A dermoscopic photograph of a skin lesion.
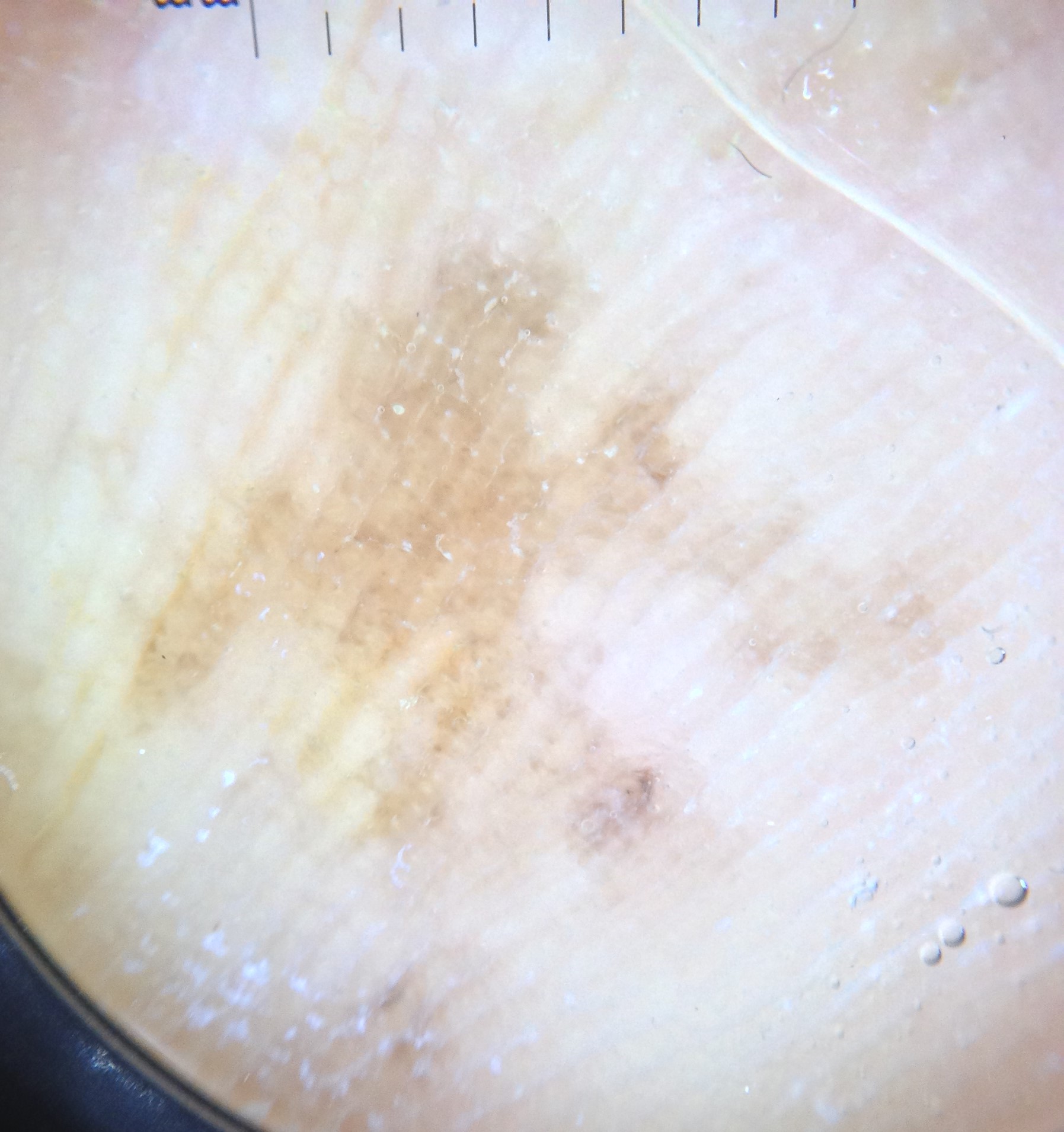Diagnosis:
Confirmed on histopathology as a malignant lesion — an acral lentiginous melanoma.